A dermatoscopic image of a skin lesion · acquired for a research image collection, with no referral diagnosis — 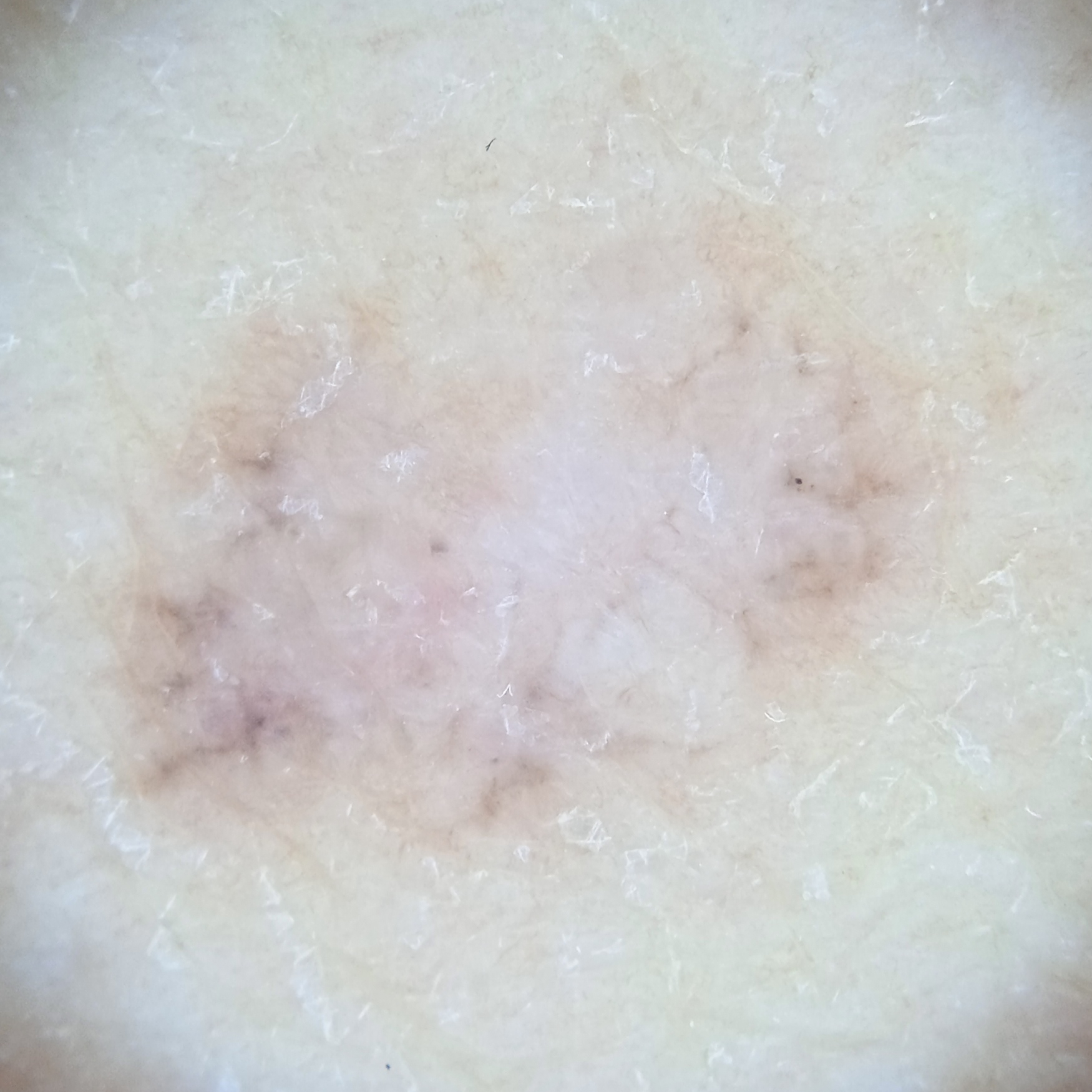Q: Lesion size?
A: 10.4 mm
Q: What was the diagnosis?
A: basal cell carcinoma (dermatologist consensus)